A clinical close-up photograph of a skin lesion. A patient in their 60s.
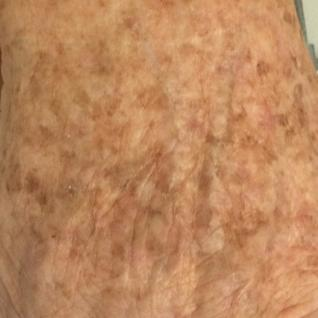The lesion was found on a forearm. By the patient's account, the lesion has not grown and has not bled. The clinical impression was a lesion of indeterminate malignant potential — an actinic keratosis.